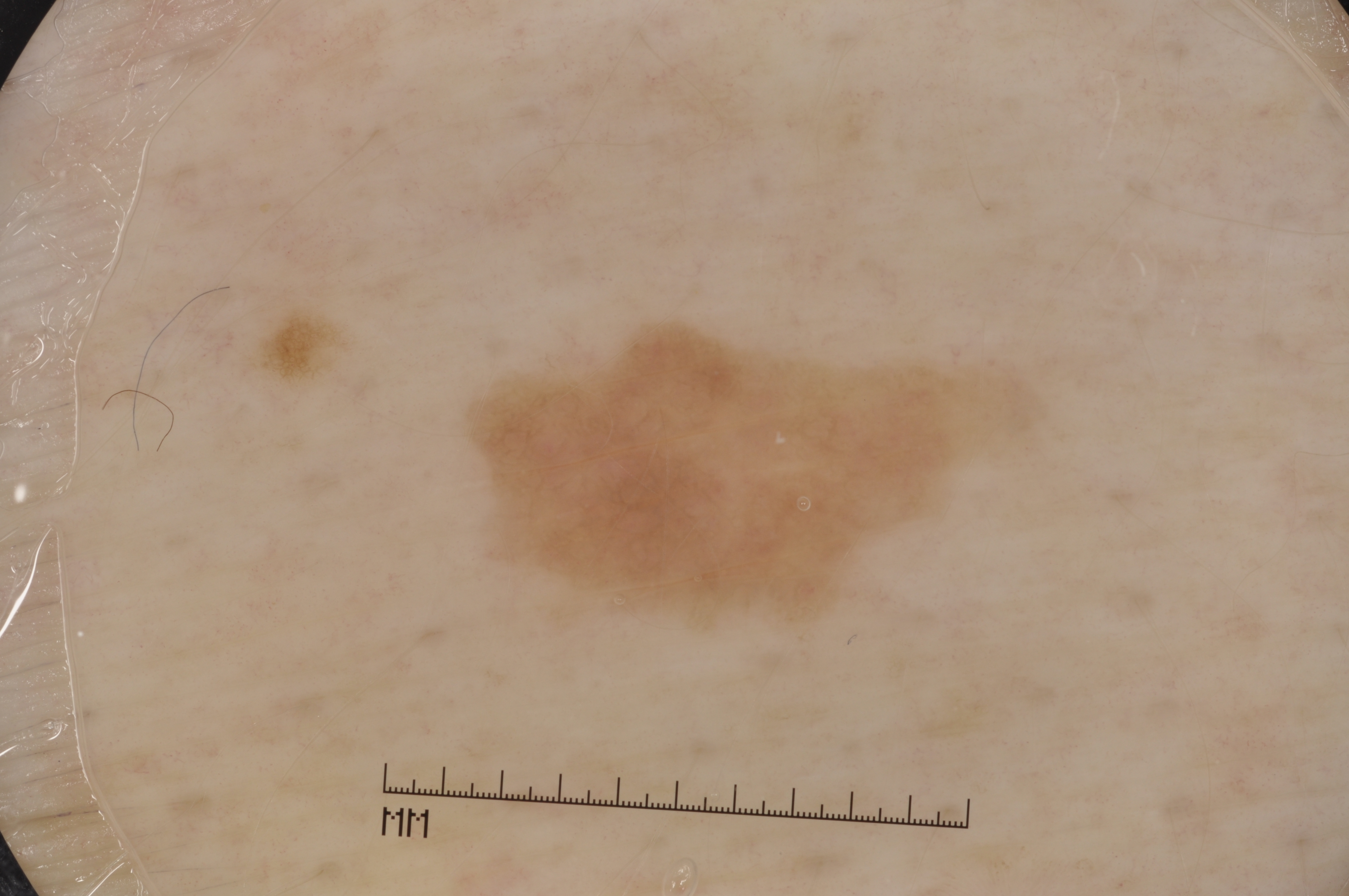Dermoscopy of a skin lesion. A female patient aged around 40. On dermoscopy, the lesion shows pigment network; no milia-like cysts, negative network, or streaks. The lesion is bounded by box(474, 322, 1033, 616). Clinically diagnosed as a seborrheic keratosis, a benign skin lesion.